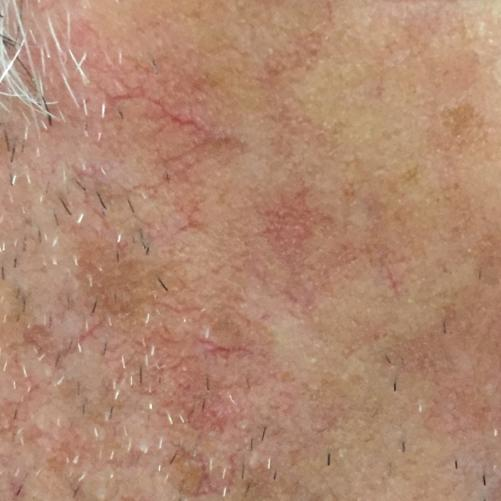The clinical impression was an actinic keratosis.